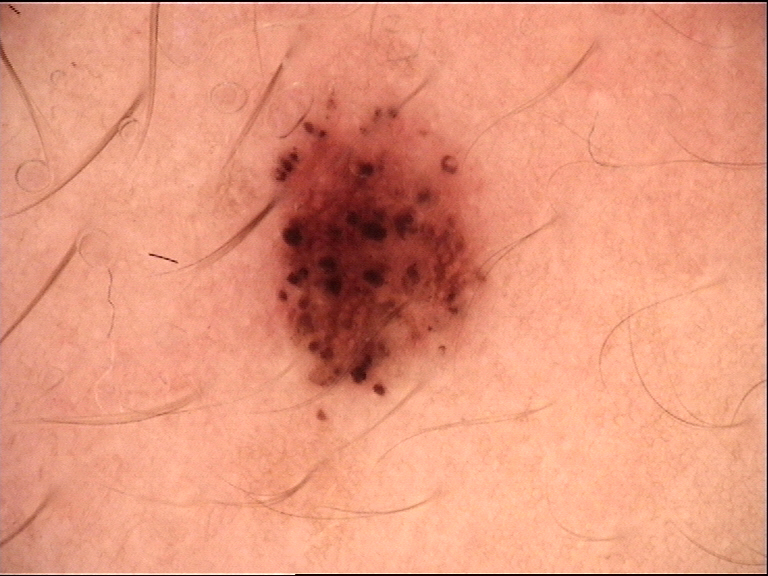A dermatoscopic image of a skin lesion. The diagnostic label was a benign lesion — a dysplastic junctional nevus.